A dermoscopic photograph of a skin lesion.
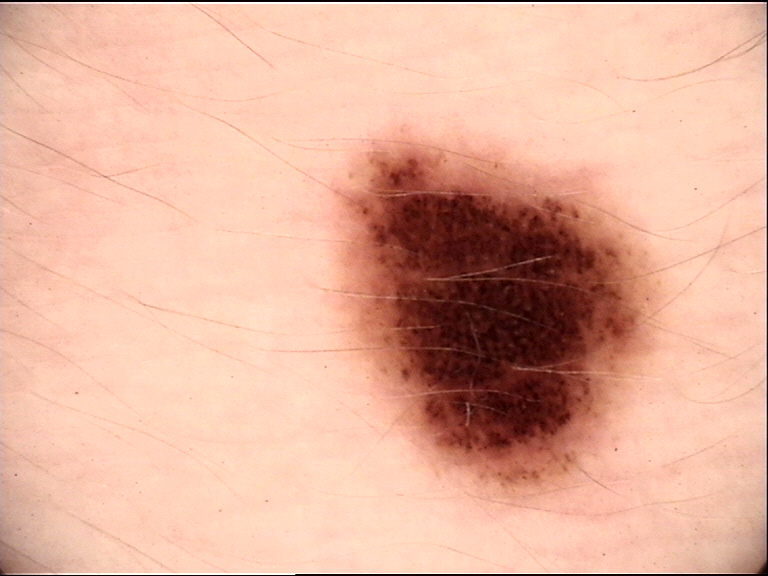Classified as a dysplastic junctional nevus.